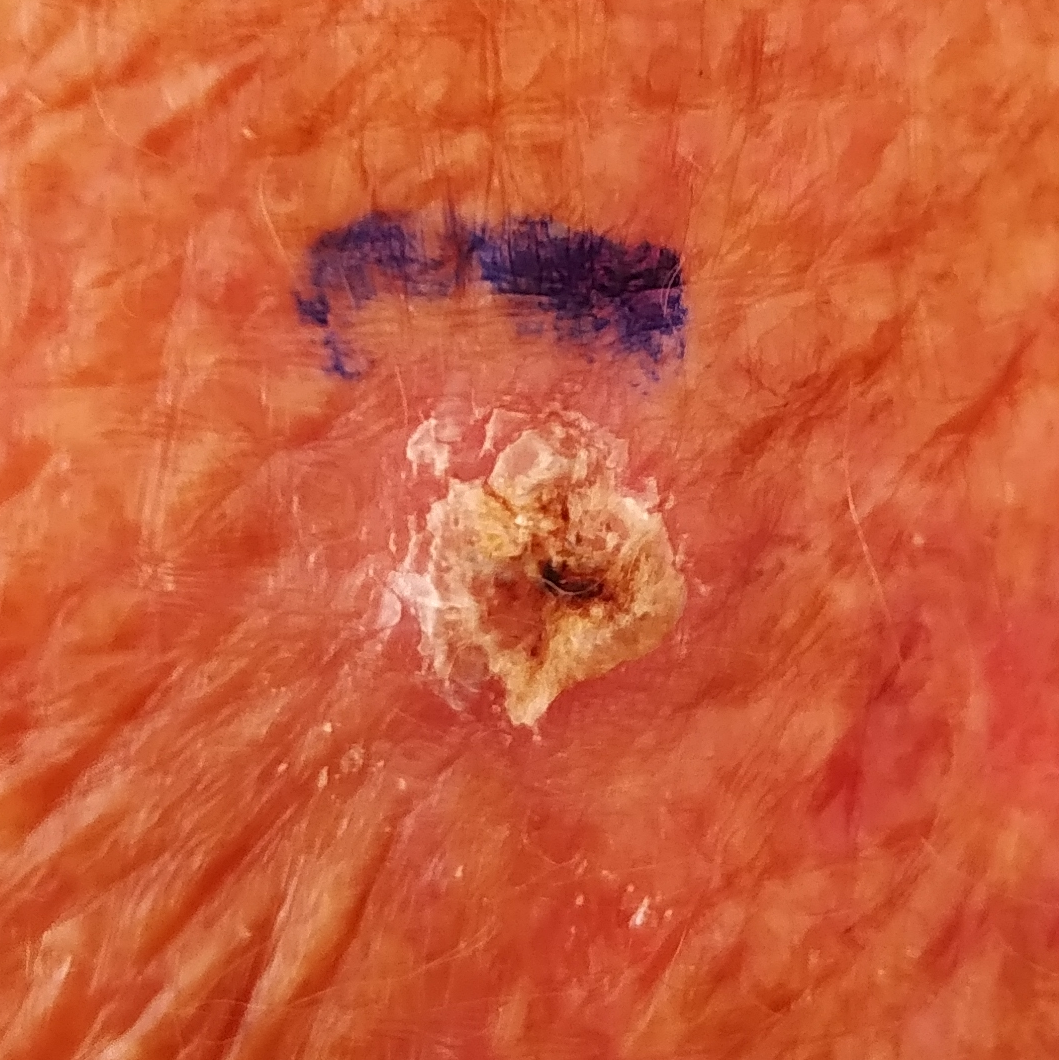A clinical close-up photograph of a skin lesion. Fitzpatrick skin type II. By history, no tobacco use and no prior malignancy (patient or family). A female subject in their early 90s. Located on a forearm. The lesion measures approximately 10 × 10 mm. By the patient's account, the lesion is elevated, has bled, and itches. Histopathological examination showed a squamous cell carcinoma.